A dermoscopic close-up of a skin lesion.
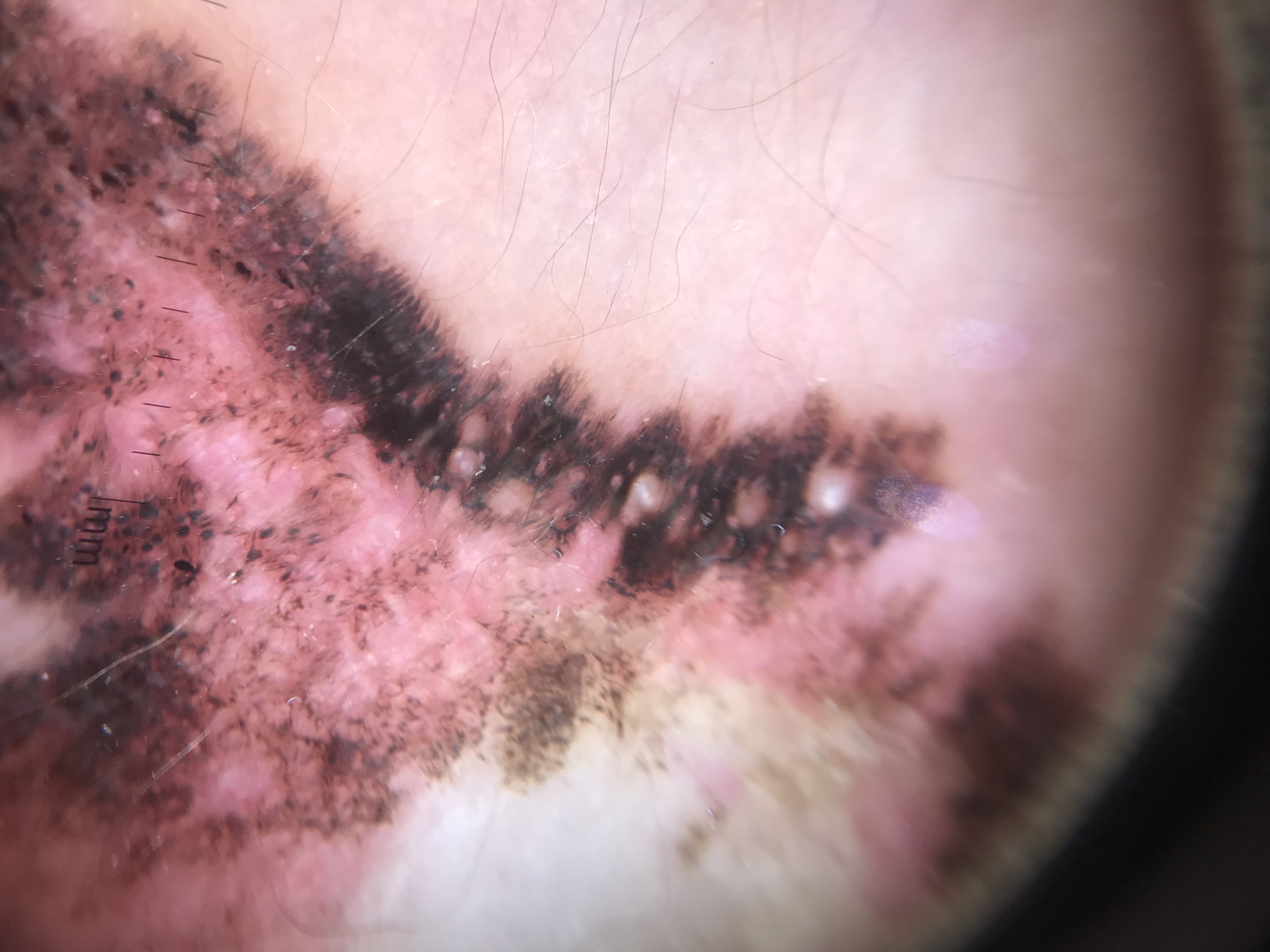label = melanoma (biopsy-proven).